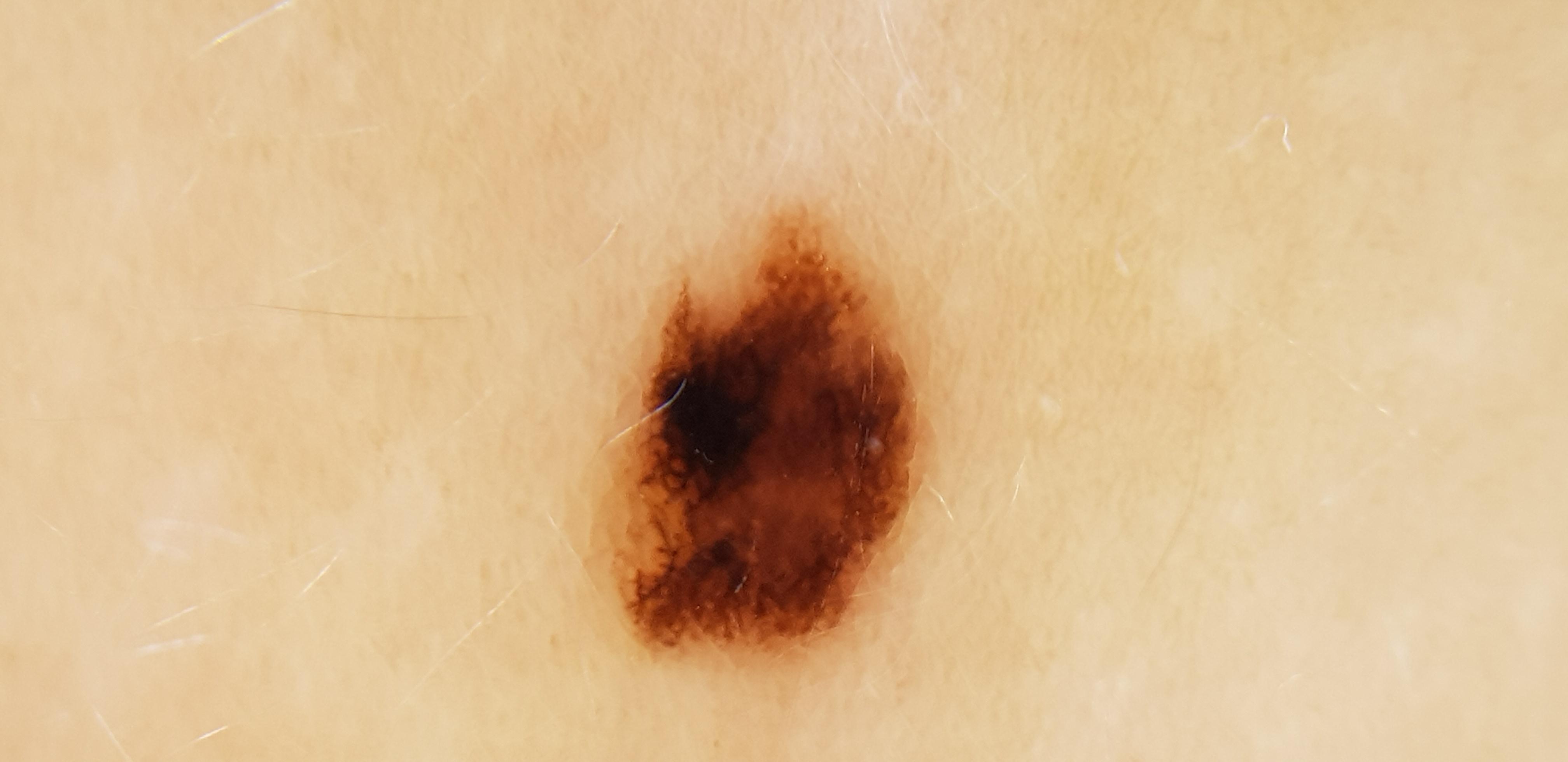{"patient": {"age_approx": 25, "sex": "female"}, "skin_type": "II", "lesion_location": {"region": "the trunk", "detail": "the posterior trunk"}, "diagnosis": {"name": "Nevus", "malignancy": "benign", "confirmation": "histopathology", "lineage": "melanocytic"}}